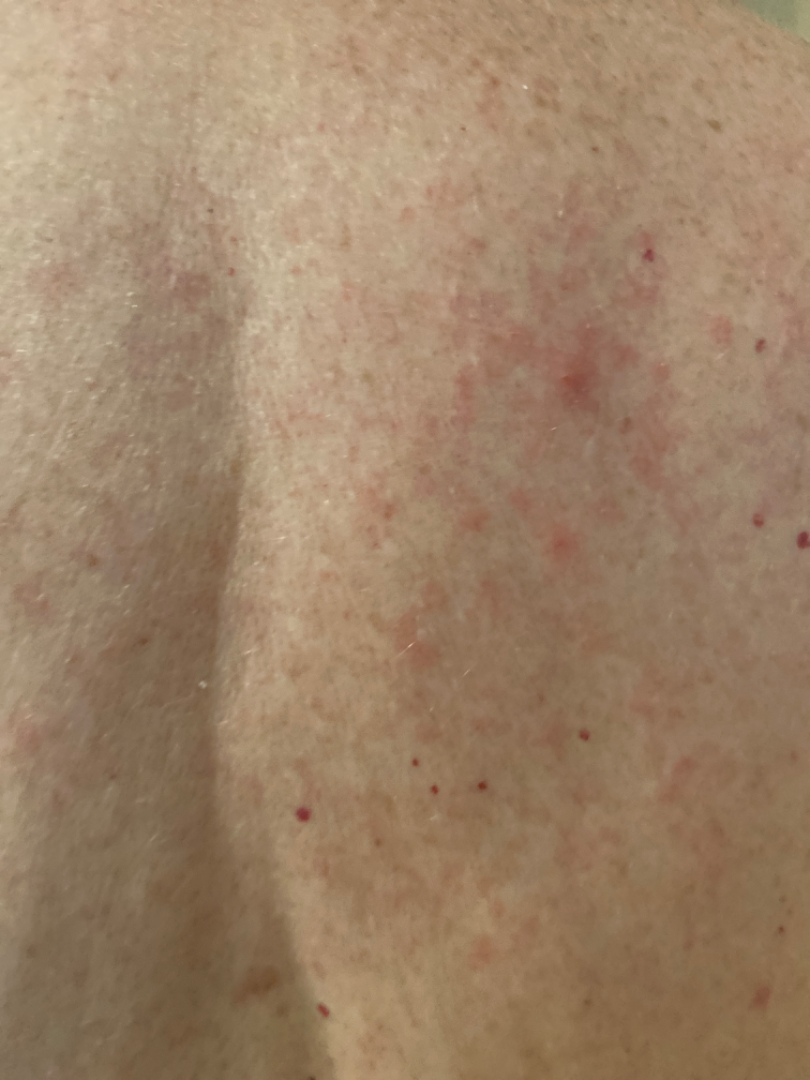Q: Could the case be diagnosed?
A: could not be assessed
Q: How was the photo taken?
A: close-up
Q: What is the affected area?
A: back of the torso and front of the torso
Q: Patient demographics?
A: female, age 70–79